The chart records a prior melanoma but no first-degree relative with melanoma · a male subject aged around 65 · the patient was assessed as Fitzpatrick II · a clinical overview photograph of a skin lesion: 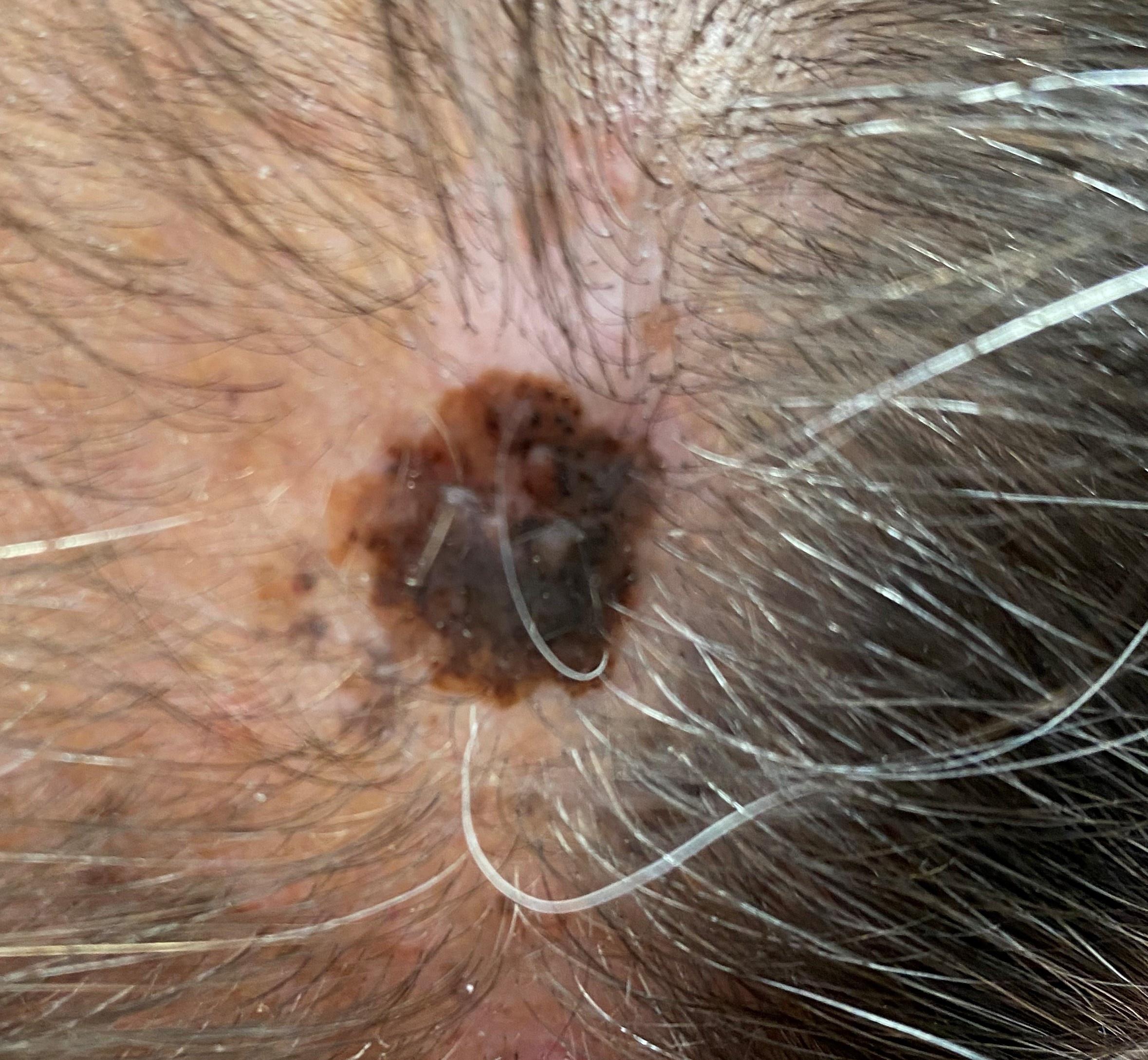Summary:
The lesion involves the head or neck.
Conclusion:
Confirmed on histopathology as a skin cancer — a melanoma.